A dermatoscopic image of a skin lesion.
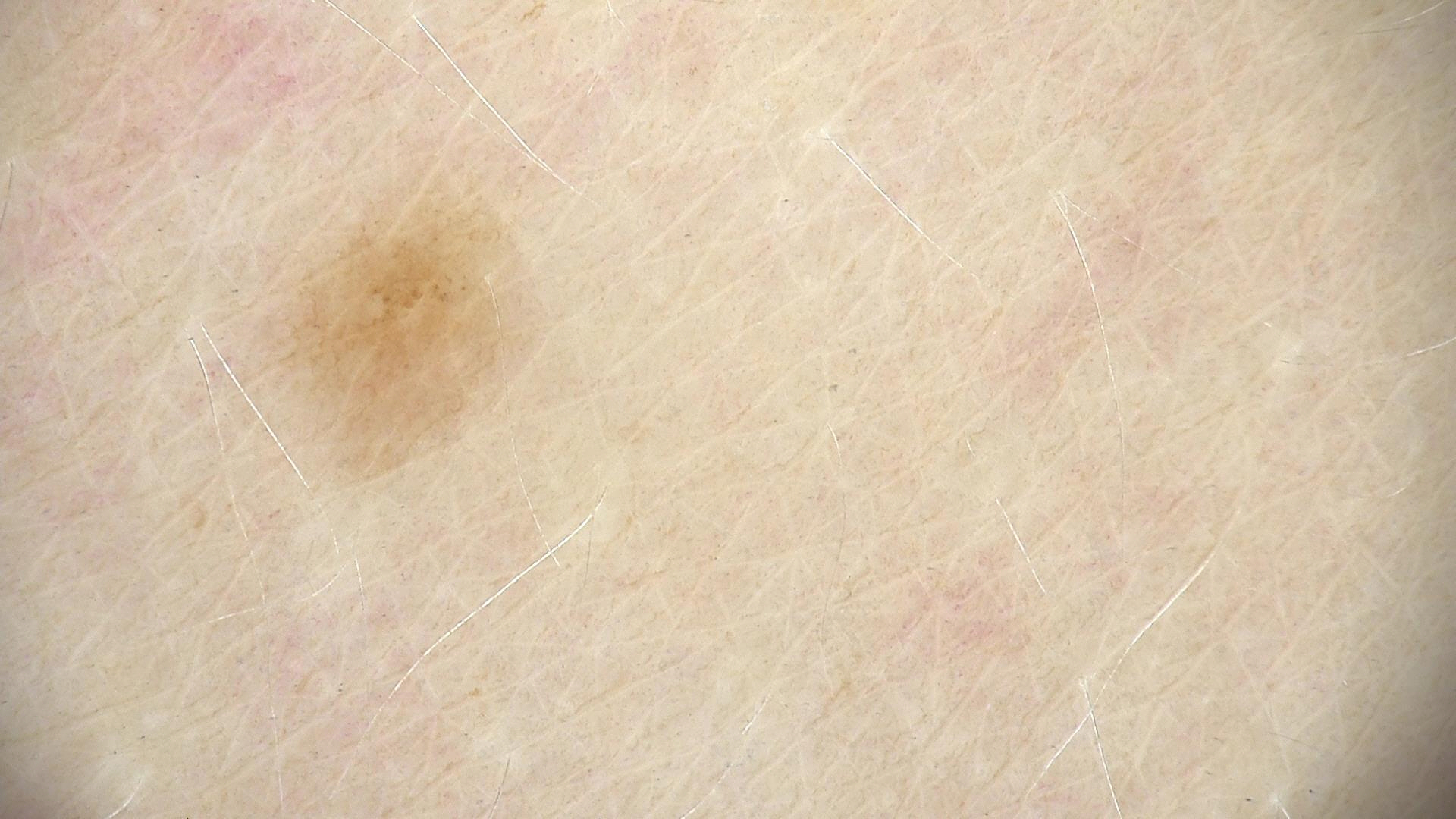assessment = dysplastic junctional nevus (expert consensus).